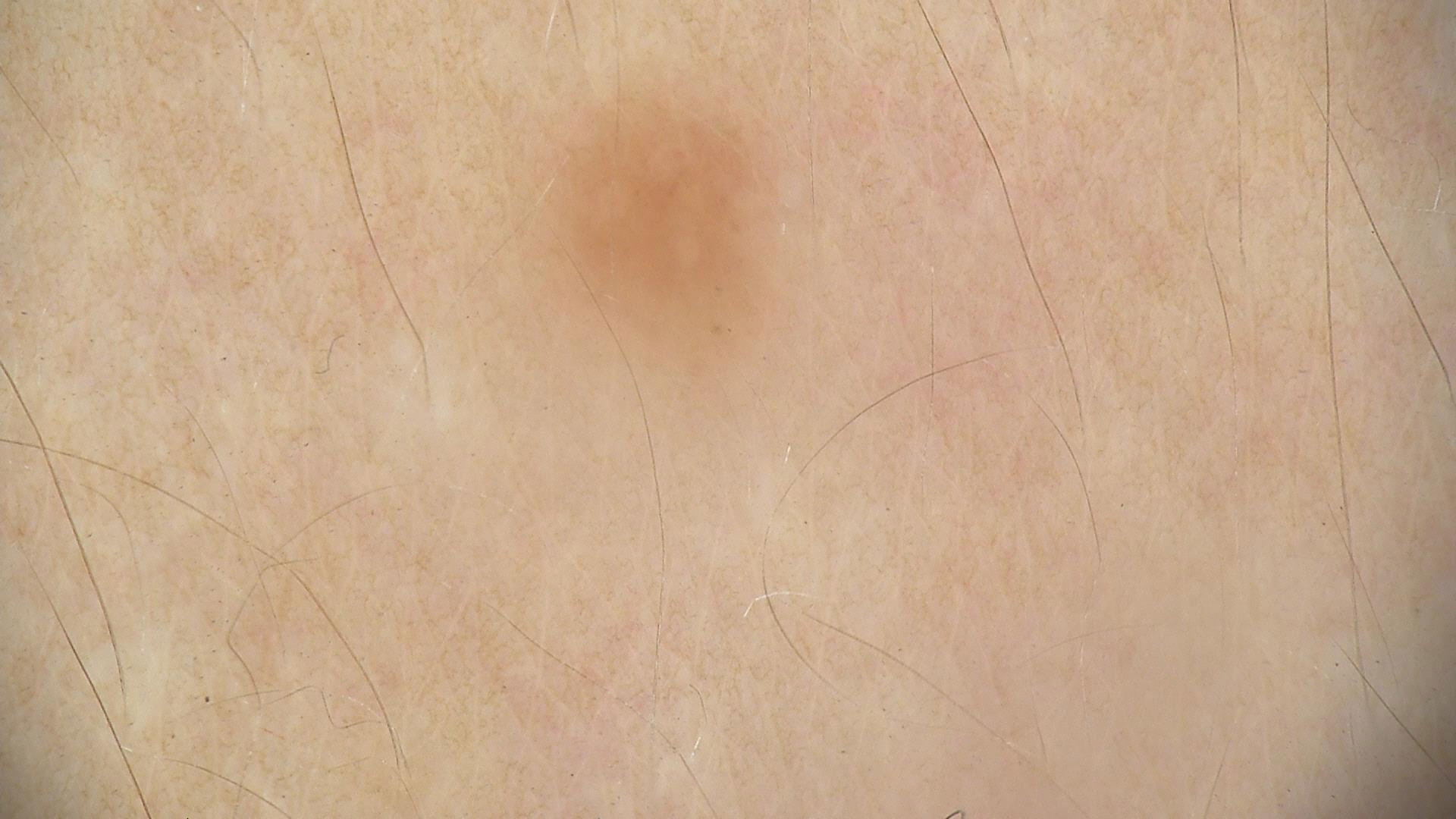Findings:
• image: dermatoscopy
• diagnostic label: dysplastic junctional nevus (expert consensus)